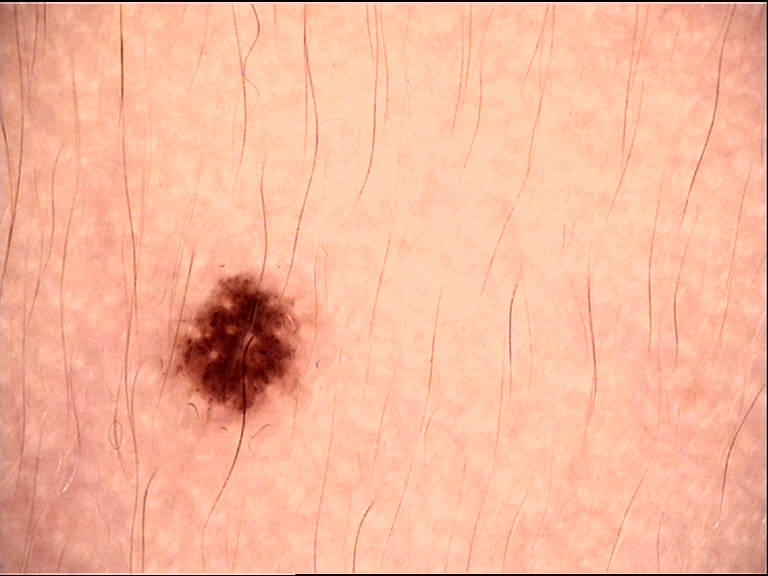A dermoscopy image of a single skin lesion. Consistent with a dysplastic junctional nevus.